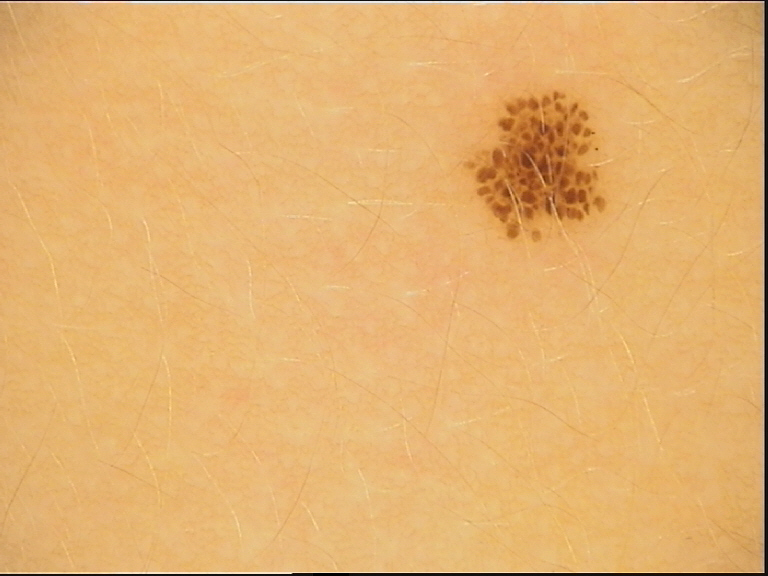Dermoscopy of a skin lesion.
The morphology is that of a banal lesion.
Classified as a junctional nevus.